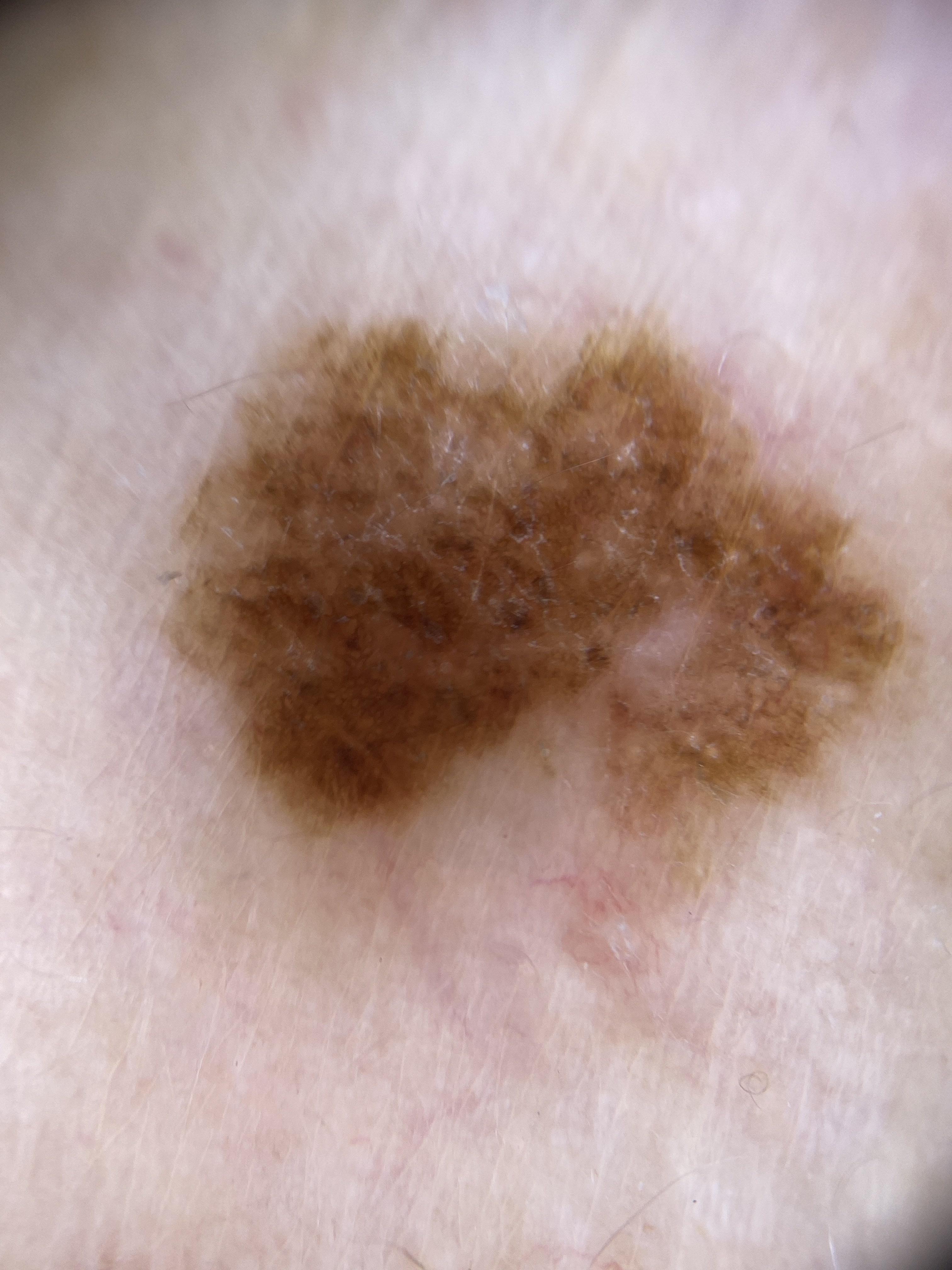Notes:
– subject: female, approximately 80 years of age
– modality: contact-polarized dermoscopy
– location: the trunk
– diagnostic label: Melanoma (biopsy-proven)